Self-categorized by the patient as a rash · the top or side of the foot and back of the hand are involved · female patient, age 18–29 · no relevant systemic symptoms · this is a close-up image · the lesion is described as flat, raised or bumpy and fluid-filled: 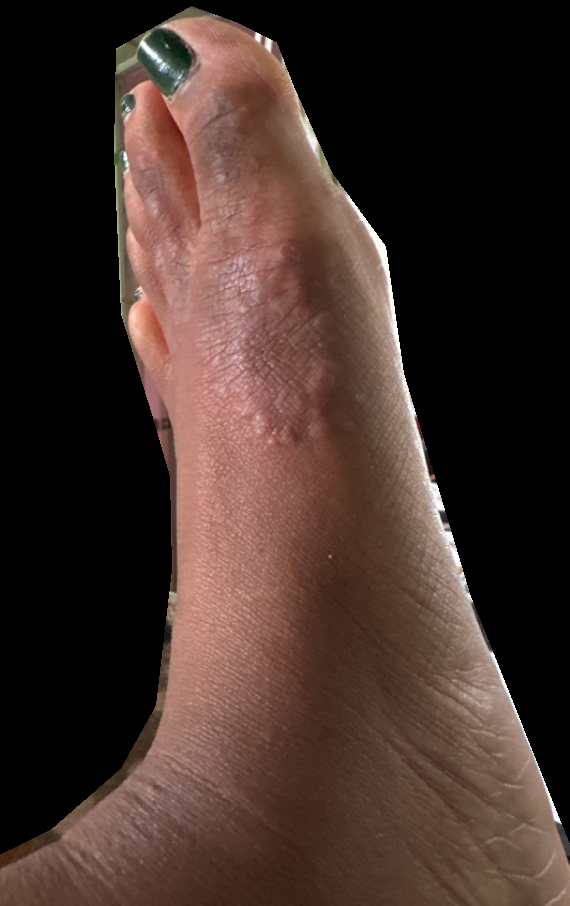The case was indeterminate on photographic review.